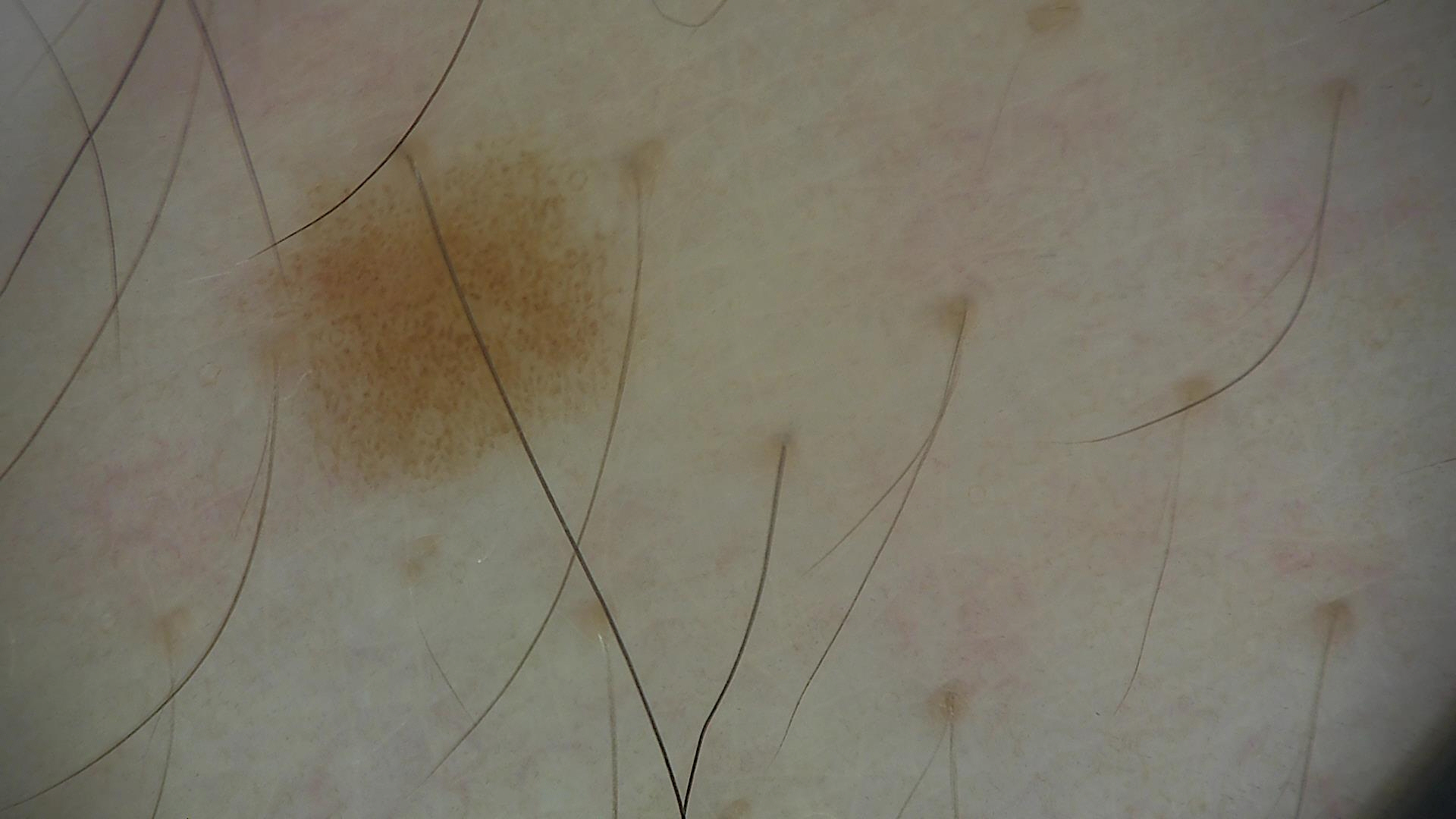Classified as a dysplastic junctional nevus.